This image was taken at an angle · the patient is 40–49, male · the lesion involves the leg — 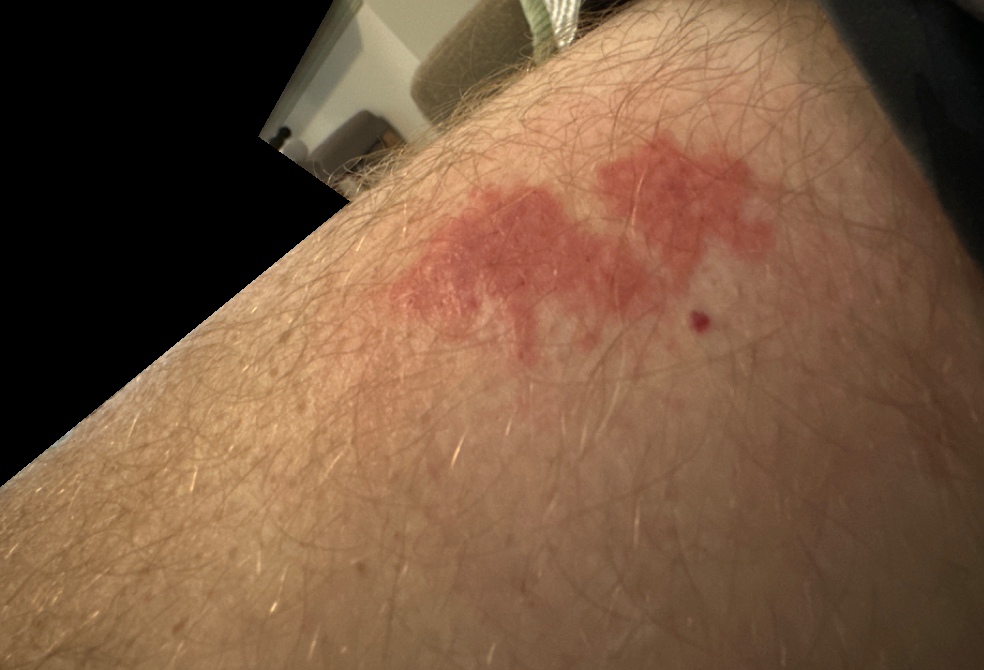{"patient_category": "a rash", "duration": "less than one week", "symptoms": "itching", "texture": "raised or bumpy", "differential": {"tied_lead": ["Inflammatory dermatosis", "SCC/SCCIS"], "unlikely": ["Skin and soft tissue atypical mycobacterial infection"]}}